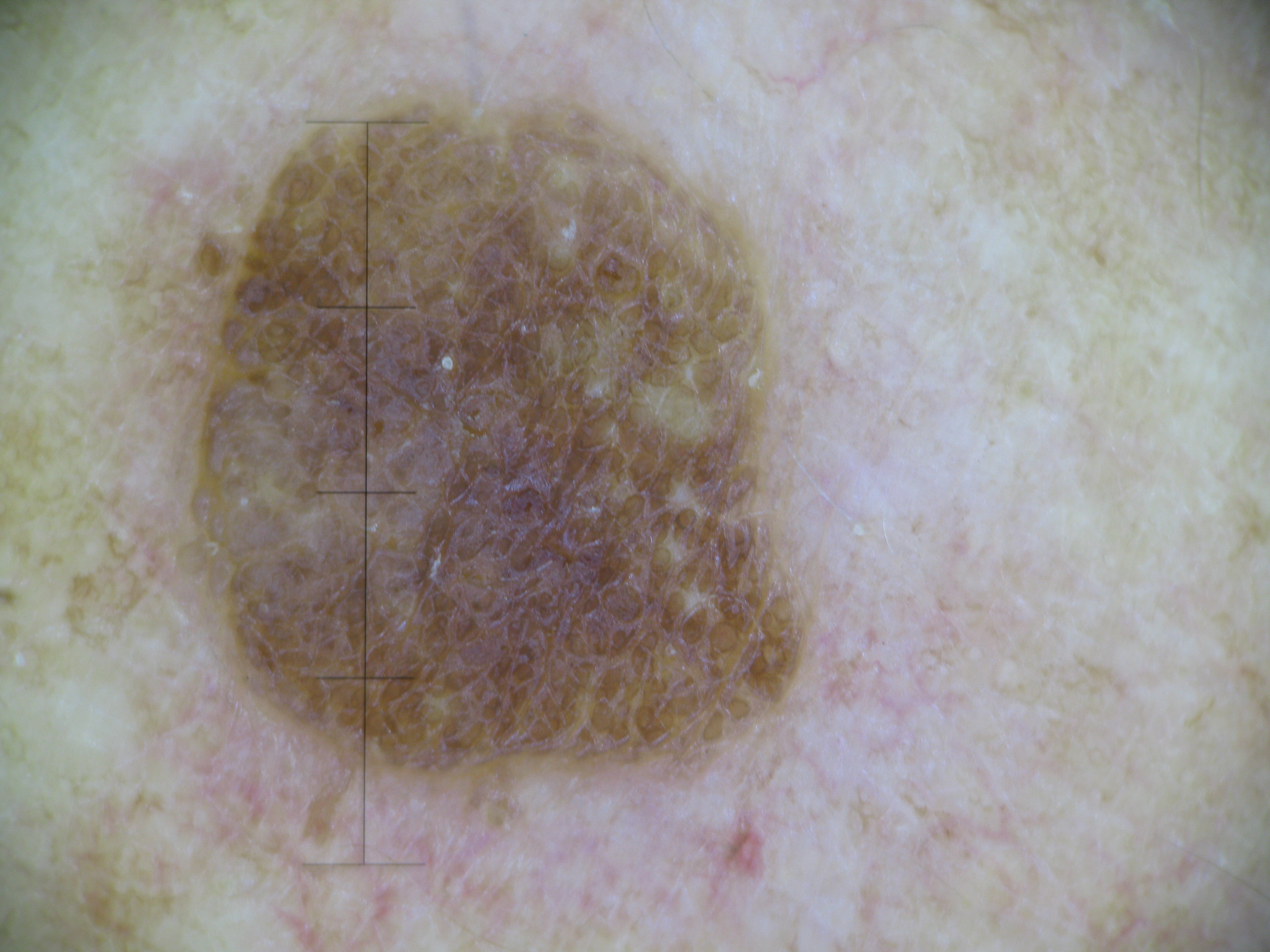The diagnosis was a seborrheic keratosis.